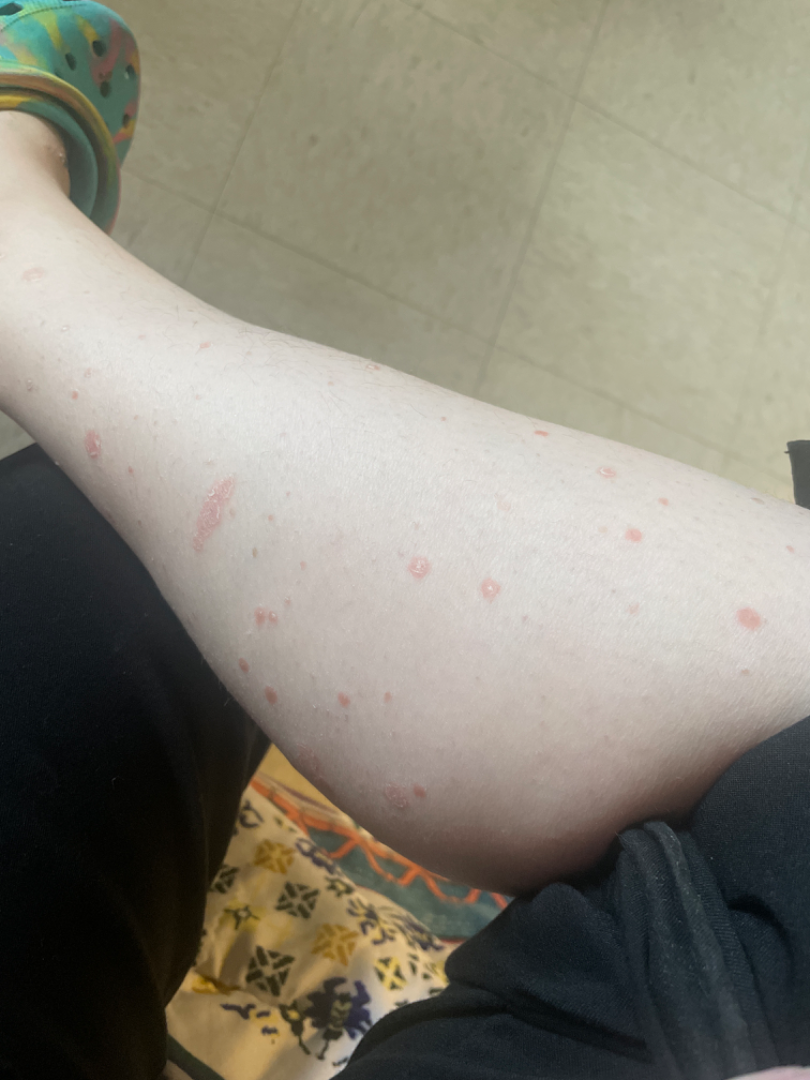texture: rough or flaky
shot_type: at a distance
body_site:
  - leg
  - arm
  - back of the hand
skin_tone:
  fitzpatrick: II
duration: one to four weeks
symptoms: itching
differential:
  Psoriasis: 1.0